The contributor notes the lesion is raised or bumpy · the patient also reports chills · the back of the torso is involved · close-up view · reported lesion symptoms include bothersome appearance, pain, enlargement and itching.
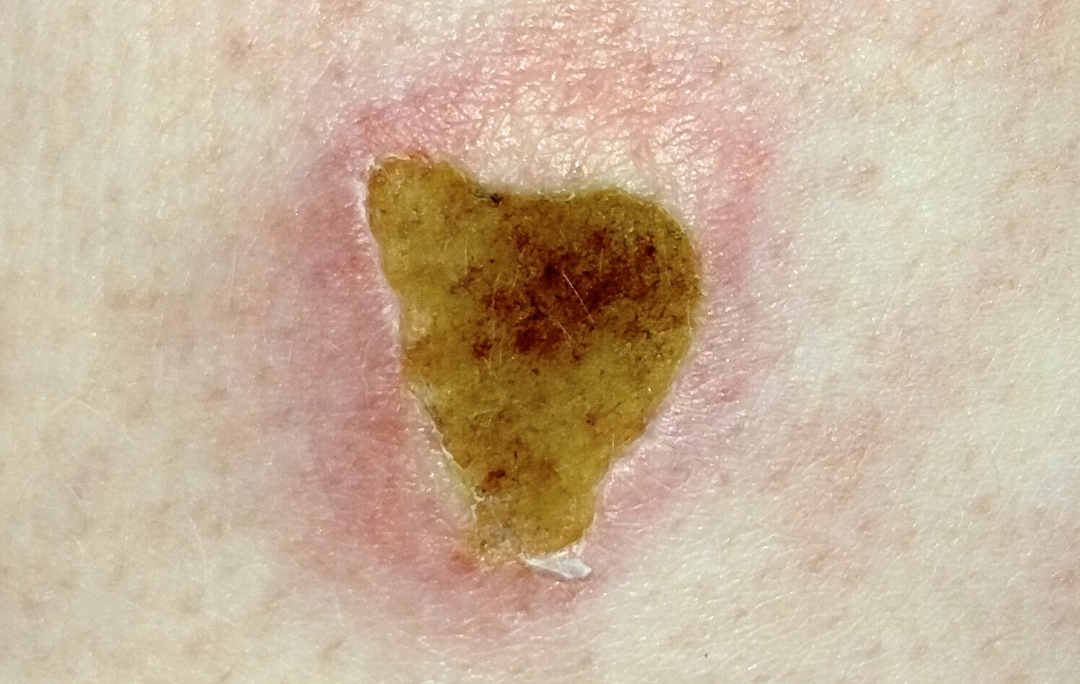Q: Could the case be diagnosed?
A: could not be assessed